Associated systemic symptoms include joint pain. The patient considered this a rash. The photograph was taken at an angle. Reported lesion symptoms include itching. Reported duration is about one day. Female patient, age 18–29:
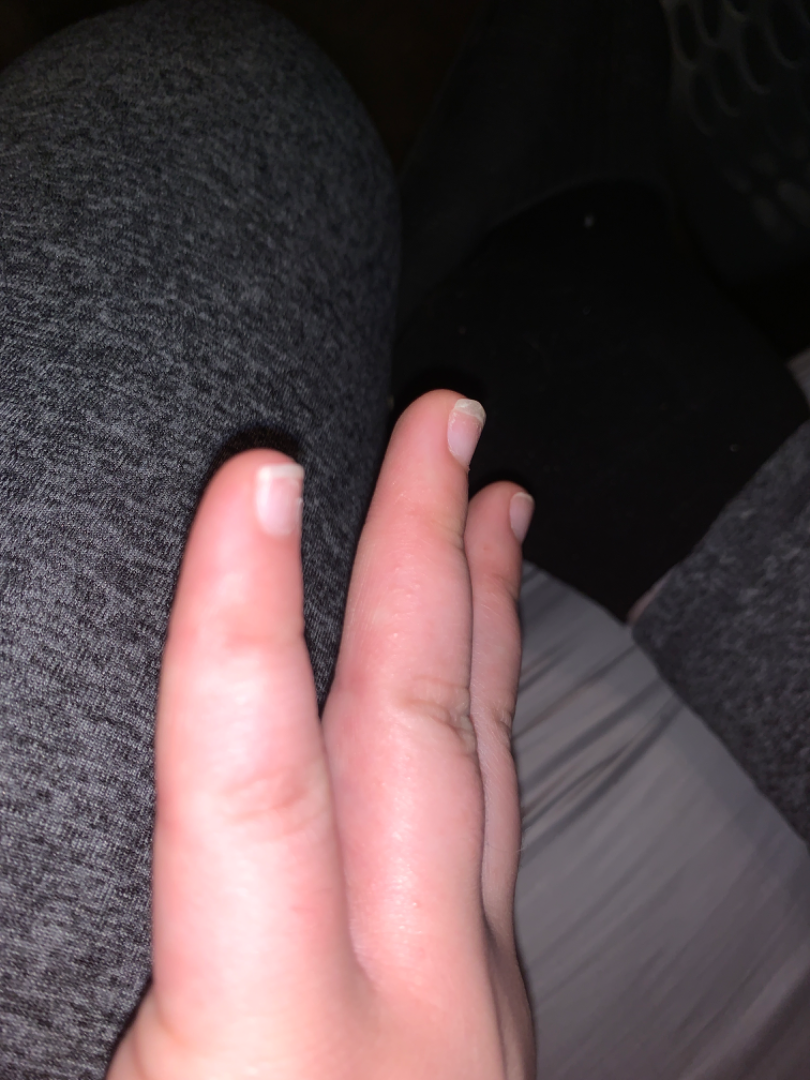dermatologist impression = favoring Eczema; a more distant consideration is Scabies; lower on the differential is Hypersensitivity.